The condition has been present for more than five years. Texture is reported as raised or bumpy and fluid-filled. The photograph was taken at a distance. The lesion involves the leg. Associated systemic symptoms include fatigue, shortness of breath and joint pain. Female contributor, age 40–49. Reported lesion symptoms include bothersome appearance and enlargement:
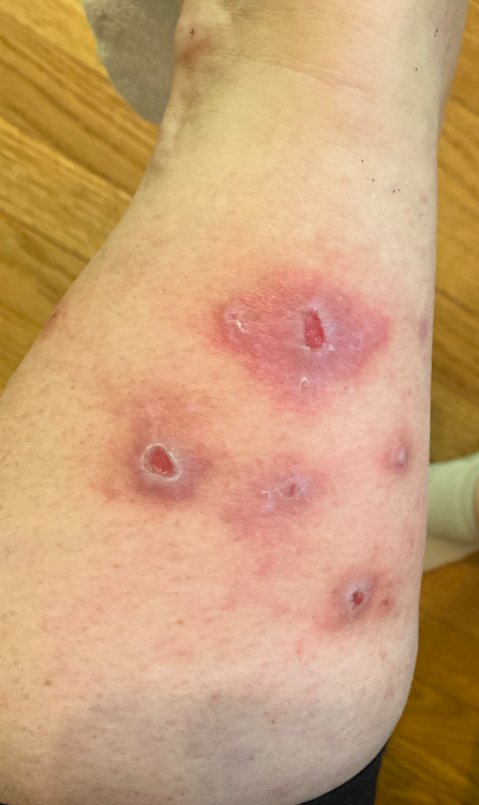Review:
The case was difficult to assess from the available photograph.